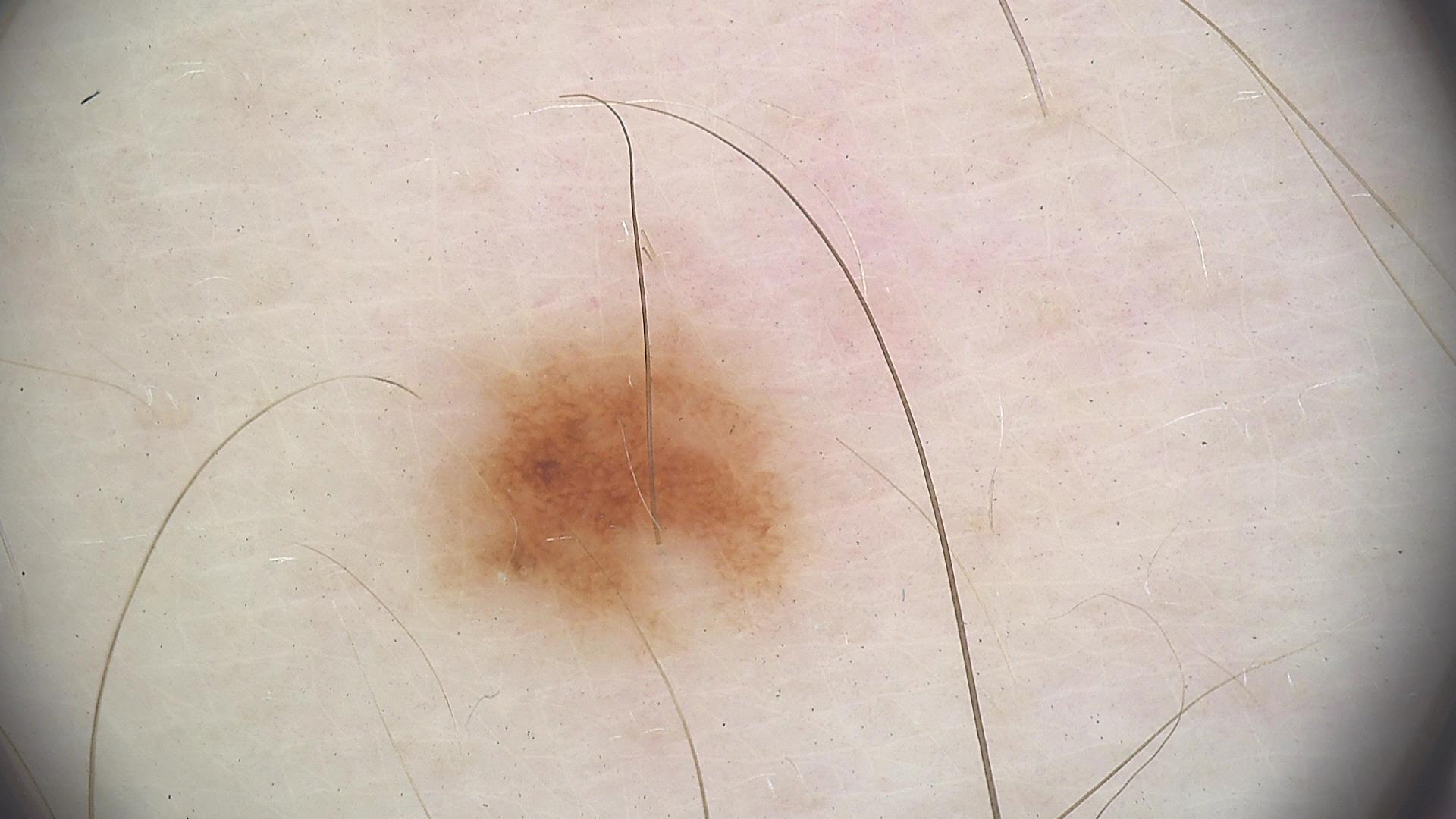A dermoscopic photograph of a skin lesion. The diagnostic label was a dysplastic junctional nevus.